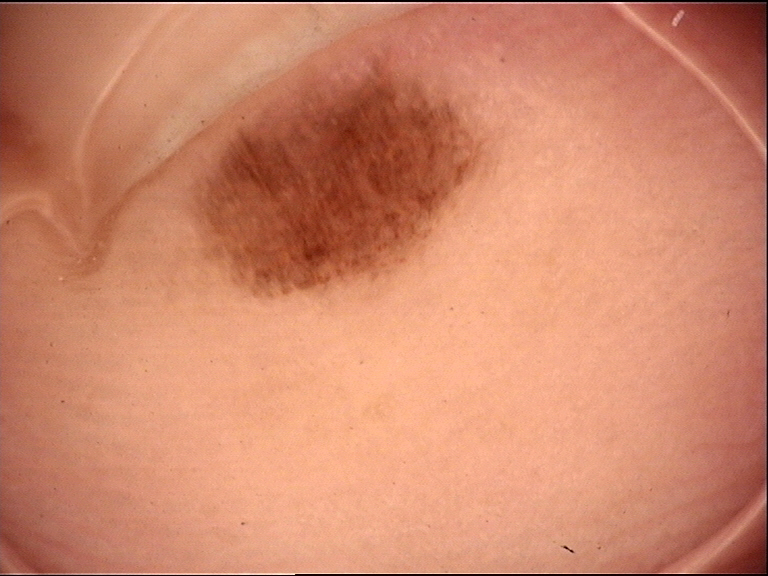A skin lesion imaged with a dermatoscope. The architecture is that of a banal lesion. The diagnostic label was an acral junctional nevus.